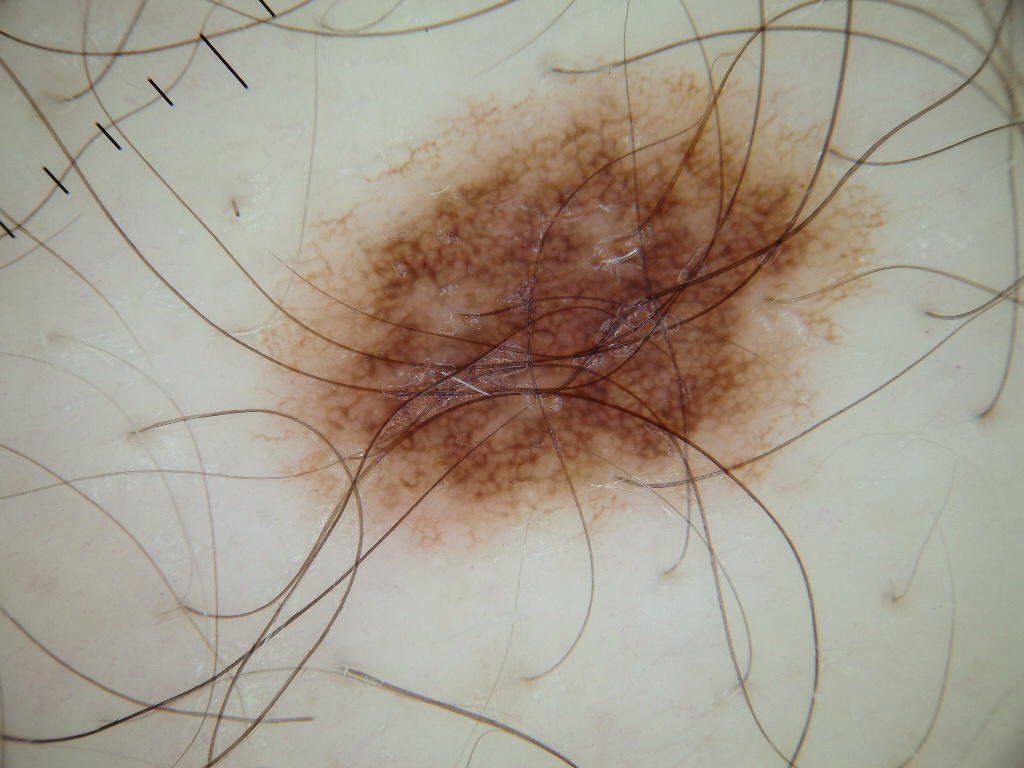  image:
    modality: dermoscopy
  patient:
    sex: male
    age_approx: 45
  lesion_location:
    bbox_xyxy:
      - 210
      - 42
      - 897
      - 565
  lesion_extent: large
  dermoscopic_features:
    present:
      - pigment network
    absent:
      - negative network
      - streaks
      - milia-like cysts
      - globules
  diagnosis:
    name: melanocytic nevus
    malignancy: benign
    lineage: melanocytic
    provenance: clinical